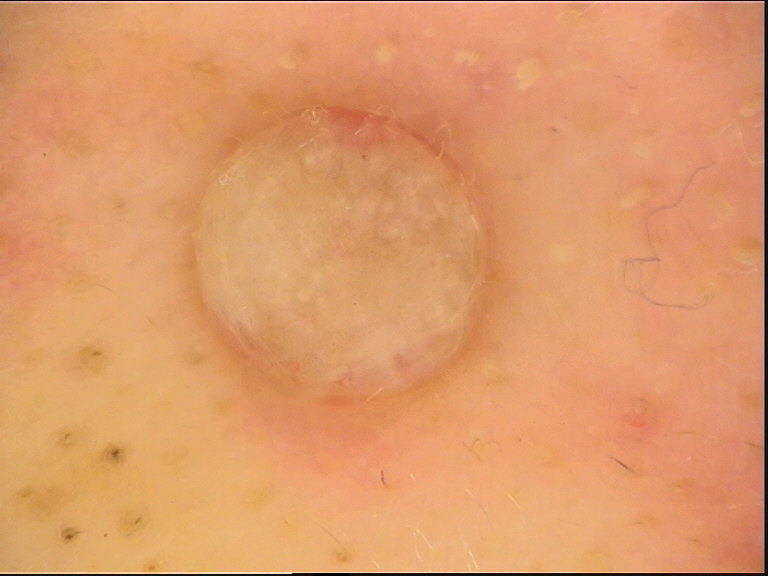Q: What is the imaging modality?
A: dermoscopy
Q: What is the lesion category?
A: banal
Q: What was the diagnostic impression?
A: dermal nevus (expert consensus)